The photograph is a close-up of the affected area, located on the leg.
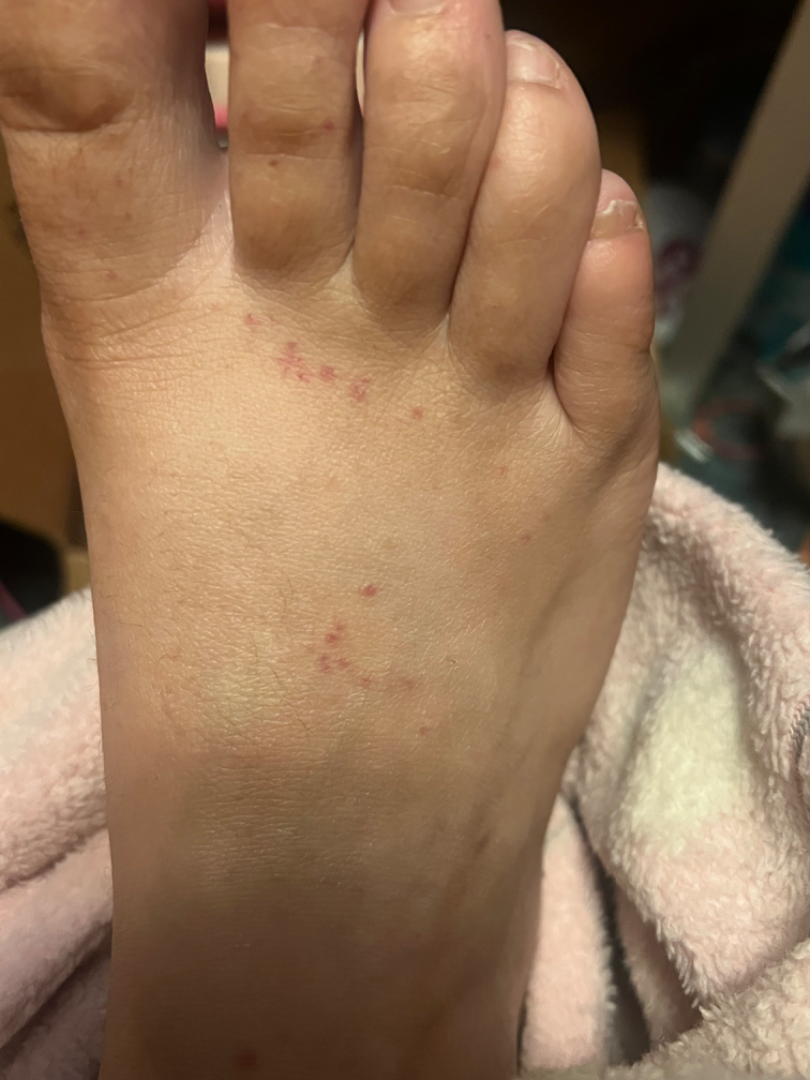impression = Insect Bite (primary); Pigmented purpuric eruption (possible); Allergic Contact Dermatitis (possible).